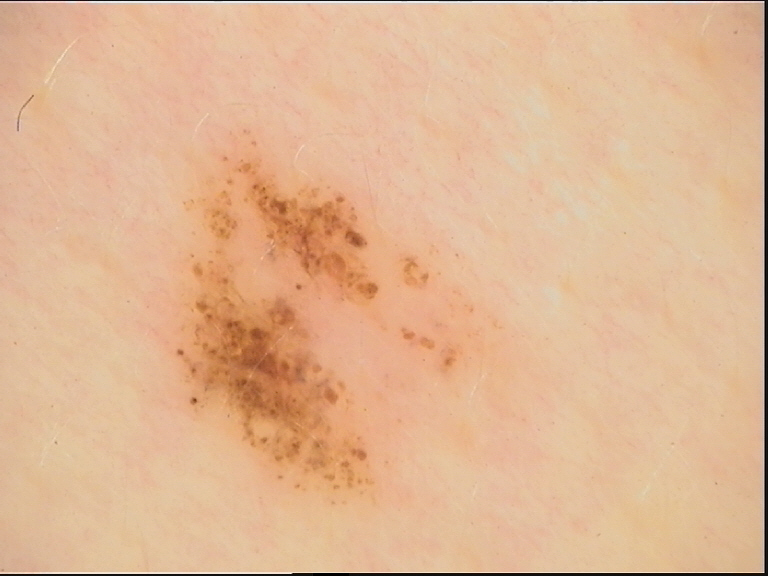Summary: A dermoscopic image of a skin lesion. Conclusion: Consistent with a benign lesion — a dysplastic compound nevus.